By self-report, a personal history of skin cancer and a personal history of cancer · a female subject aged 75 · the patient describes having a moderate number of moles · a macroscopic clinical photograph of a skin lesion.
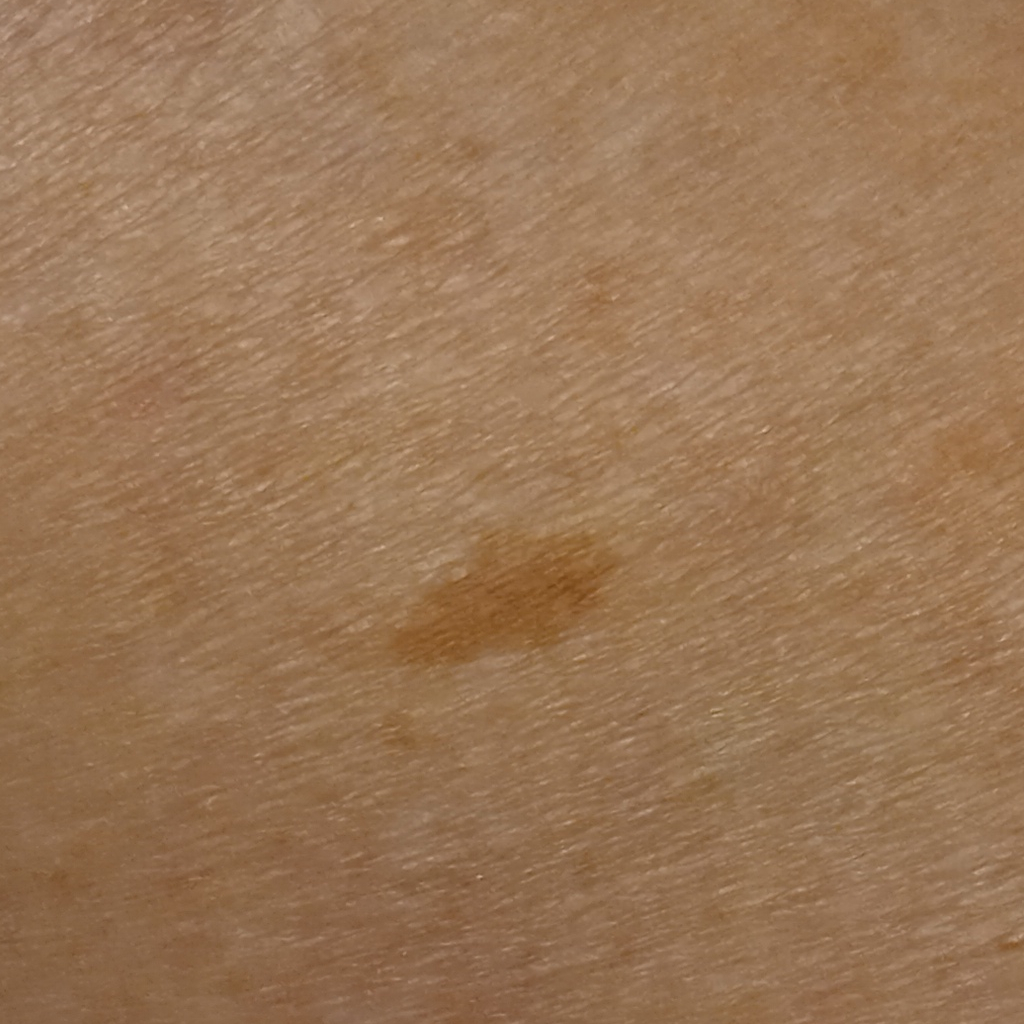The lesion involves a leg. The lesion measures approximately 8.2 mm. The diagnostic impression was a melanocytic nevus.